A dermoscopy image of a single skin lesion.
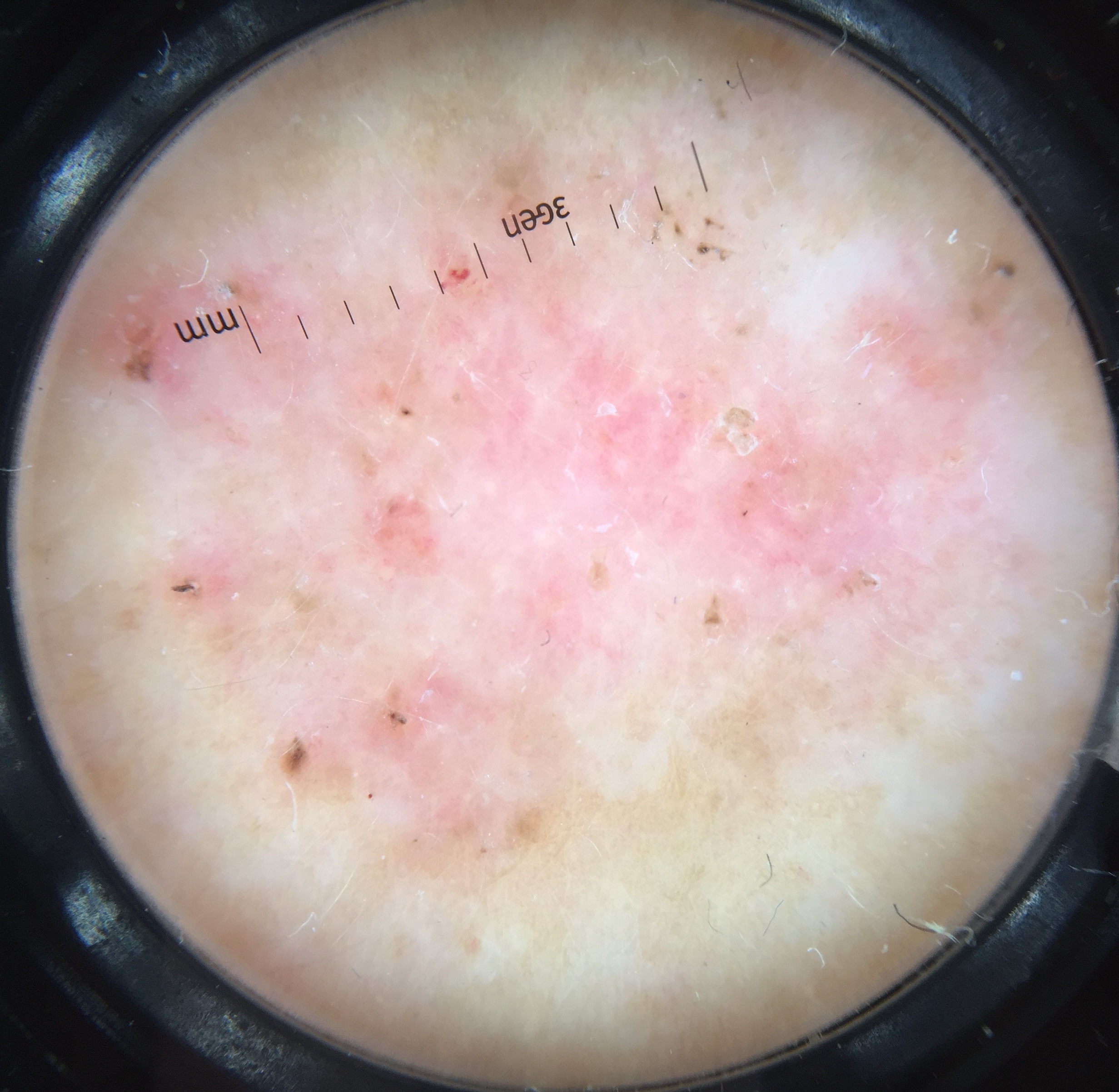Case:
The architecture is that of a keratinocytic lesion.
Conclusion:
Histopathologically confirmed as a skin cancer — a basal cell carcinoma.